A dermatoscopic image of a skin lesion:
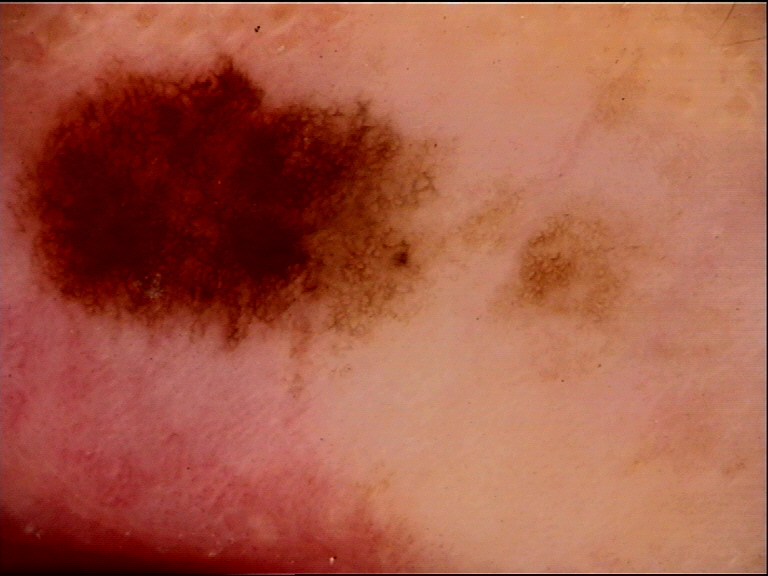Q: What was the diagnostic impression?
A: dysplastic junctional nevus (expert consensus)